A female patient age 26. Collected as part of a research study, without a referral diagnosis — 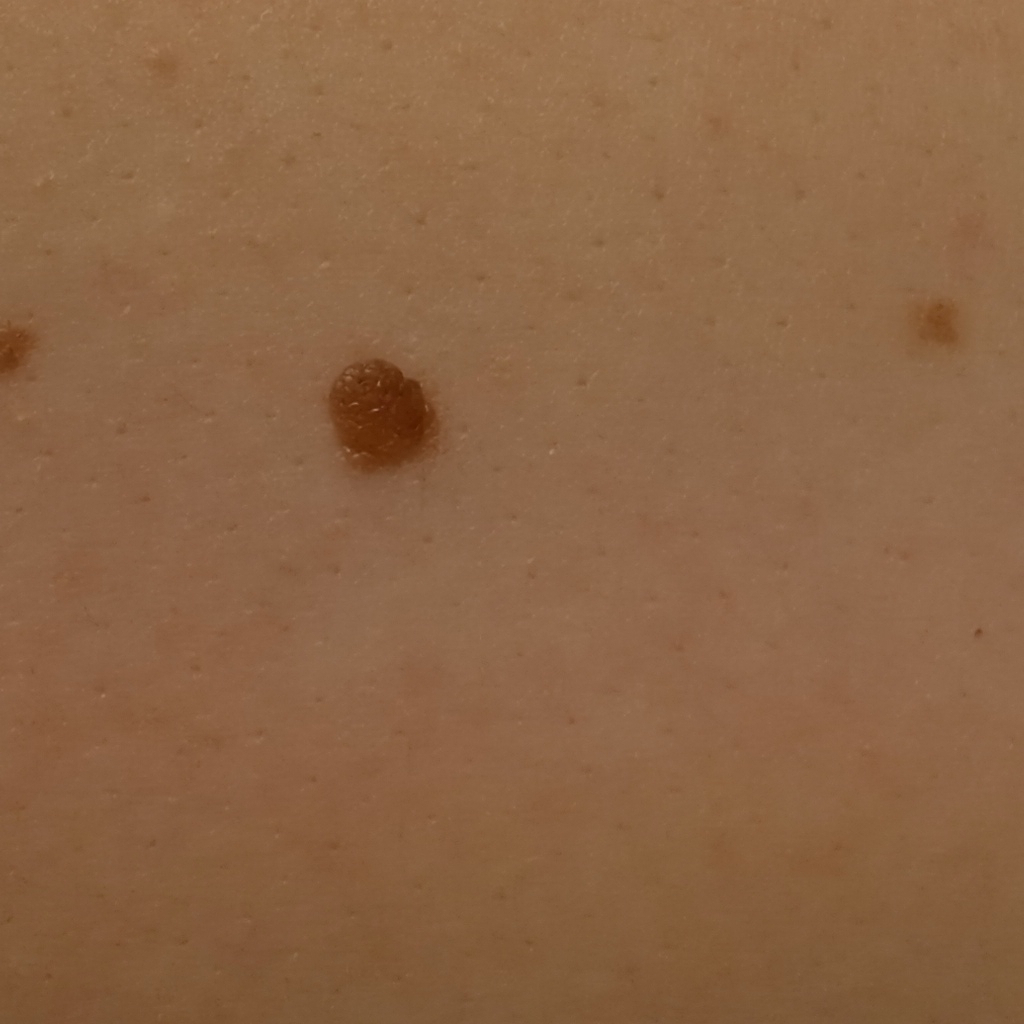site: the back | diagnosis: melanocytic nevus (dermatologist consensus).